A skin lesion imaged with a dermatoscope.
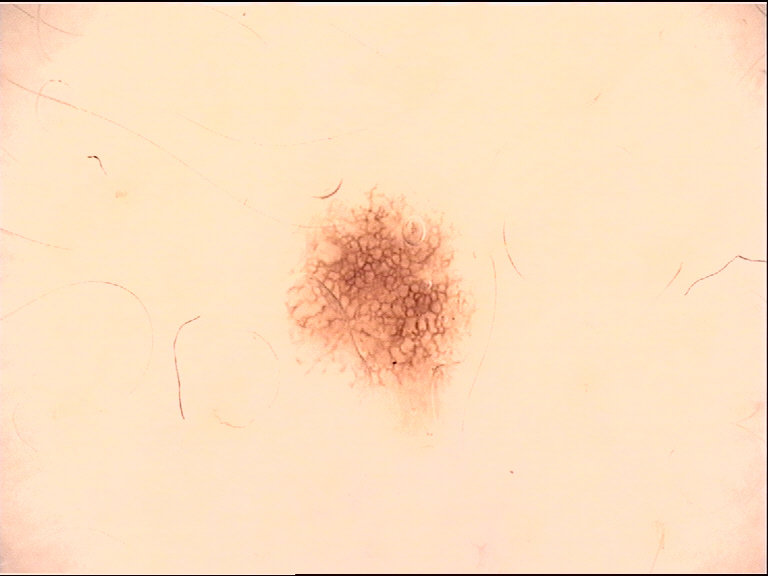The diagnostic label was a dysplastic junctional nevus.